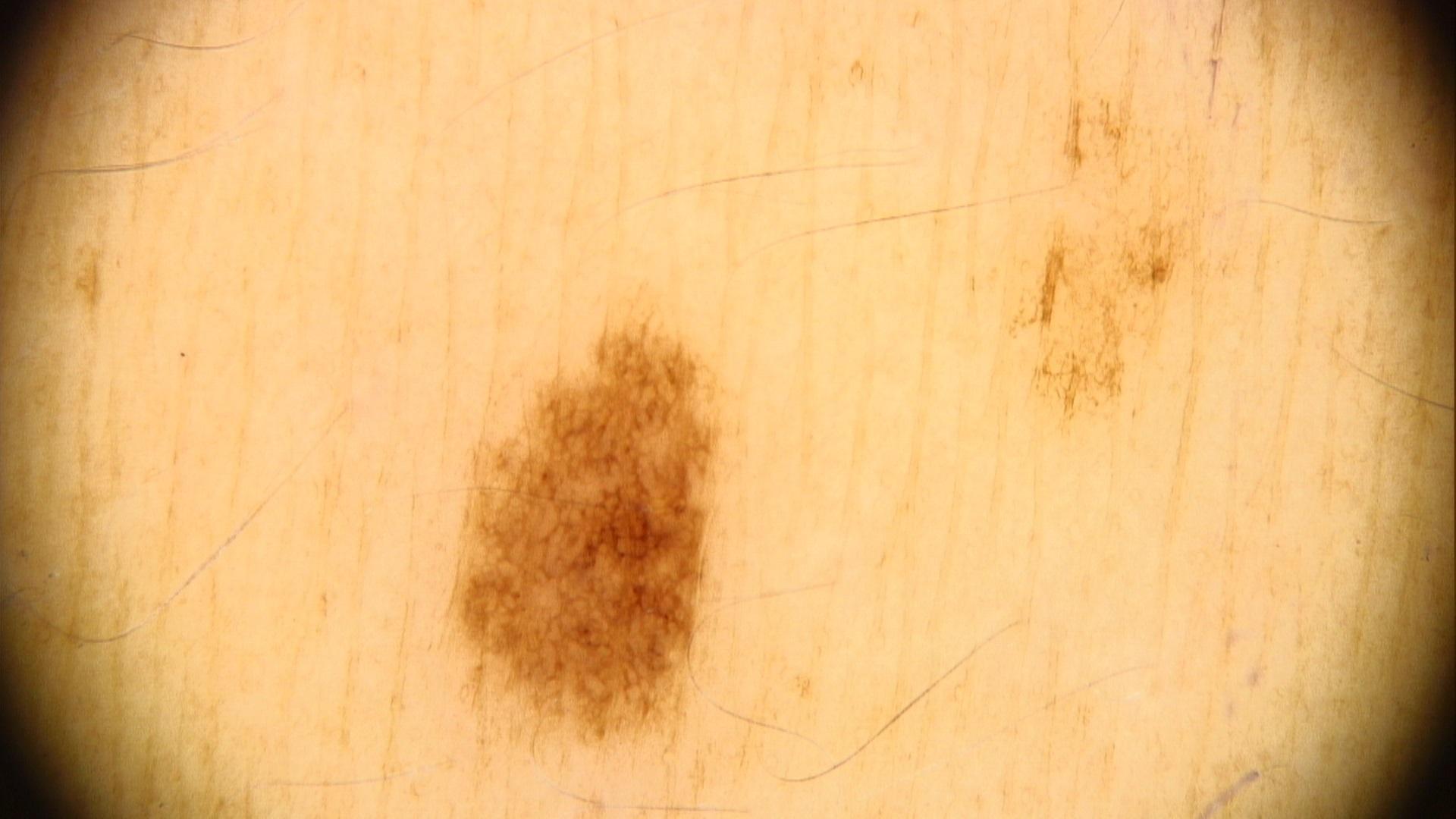modality: contact-polarized dermoscopy; subject: female, about 35 years old; risk factors: melanoma in a first-degree relative but no prior melanoma; location: a lower extremity; diagnosis: Nevus (clinical impression).